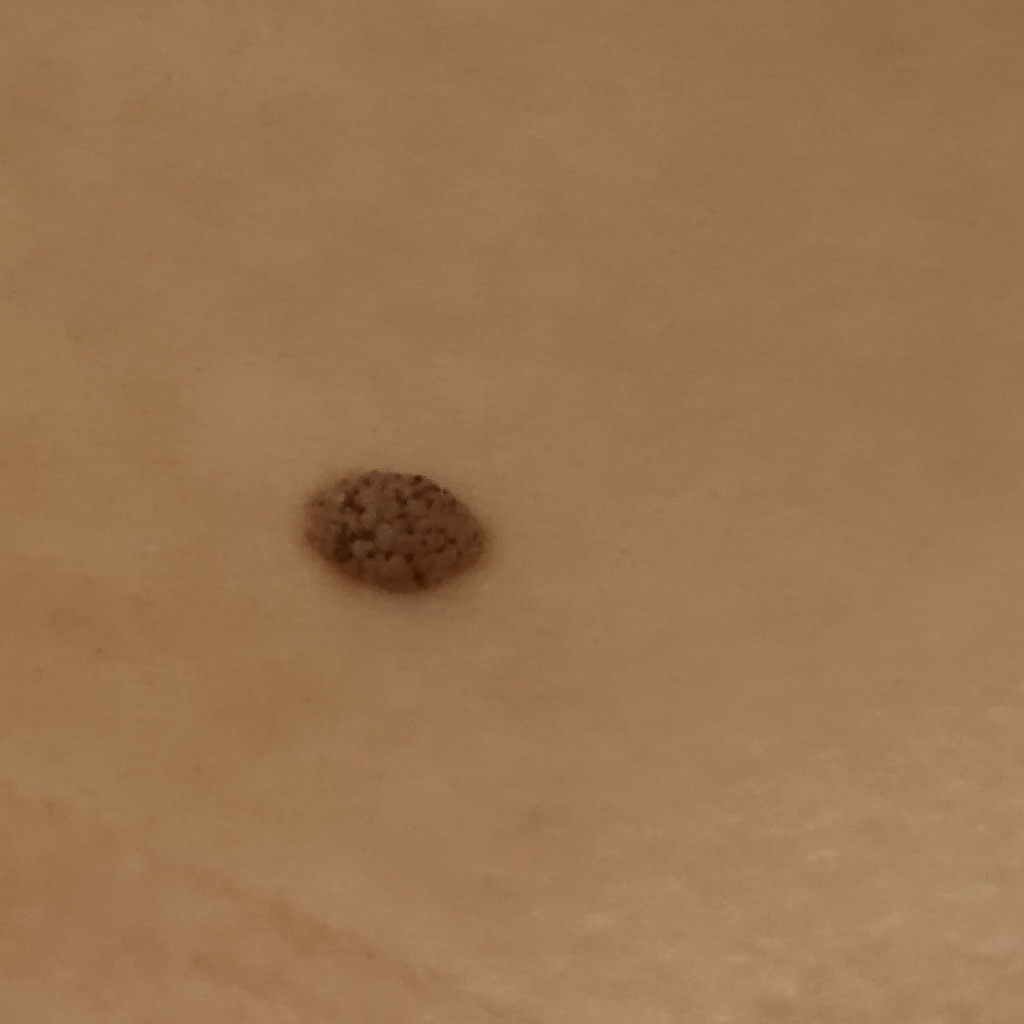assessment: seborrheic keratosis (dermatologist consensus).